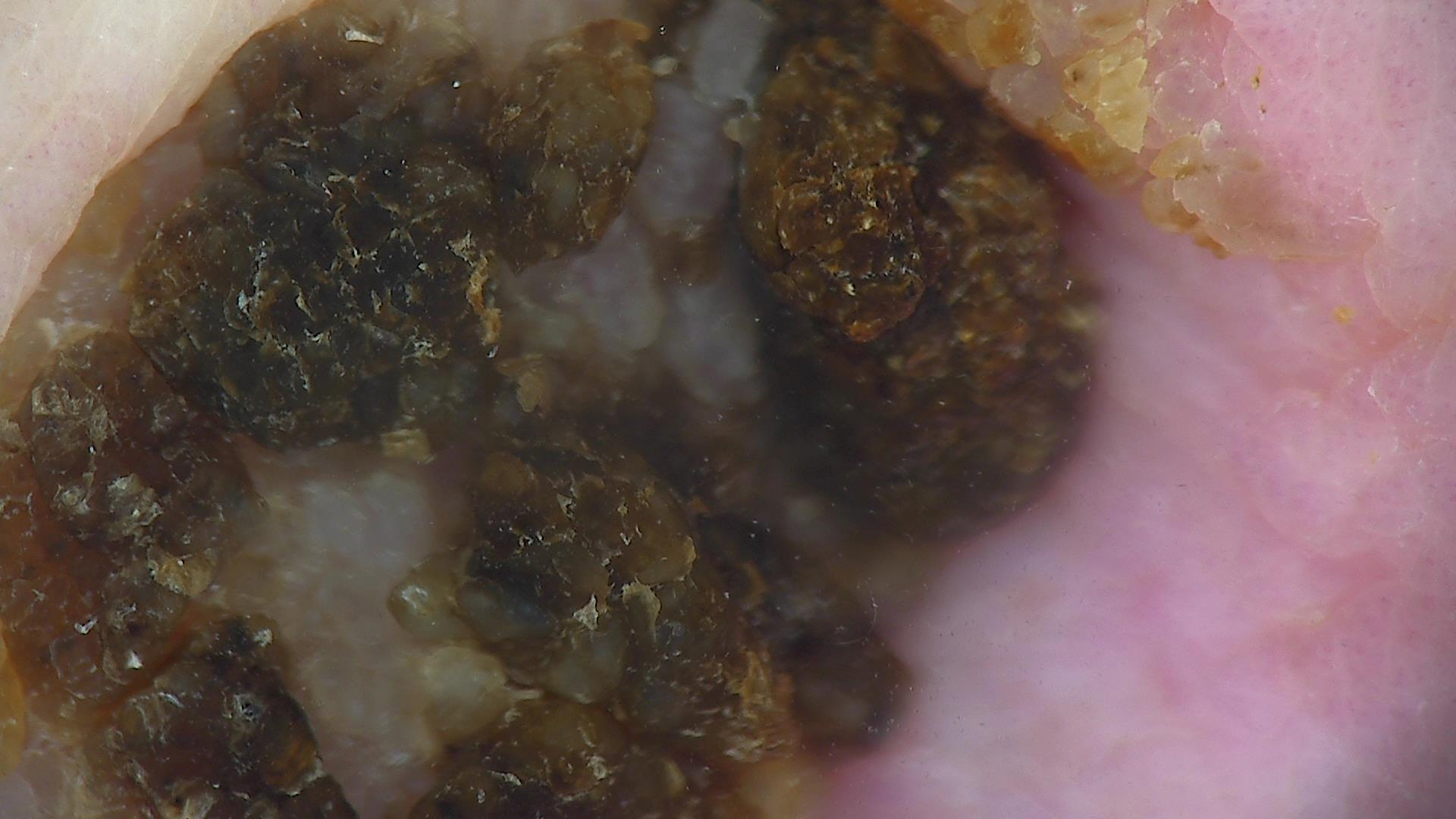Findings:
A dermoscopic image of a skin lesion.
Impression:
Classified as a keratinocytic lesion — a seborrheic keratosis.